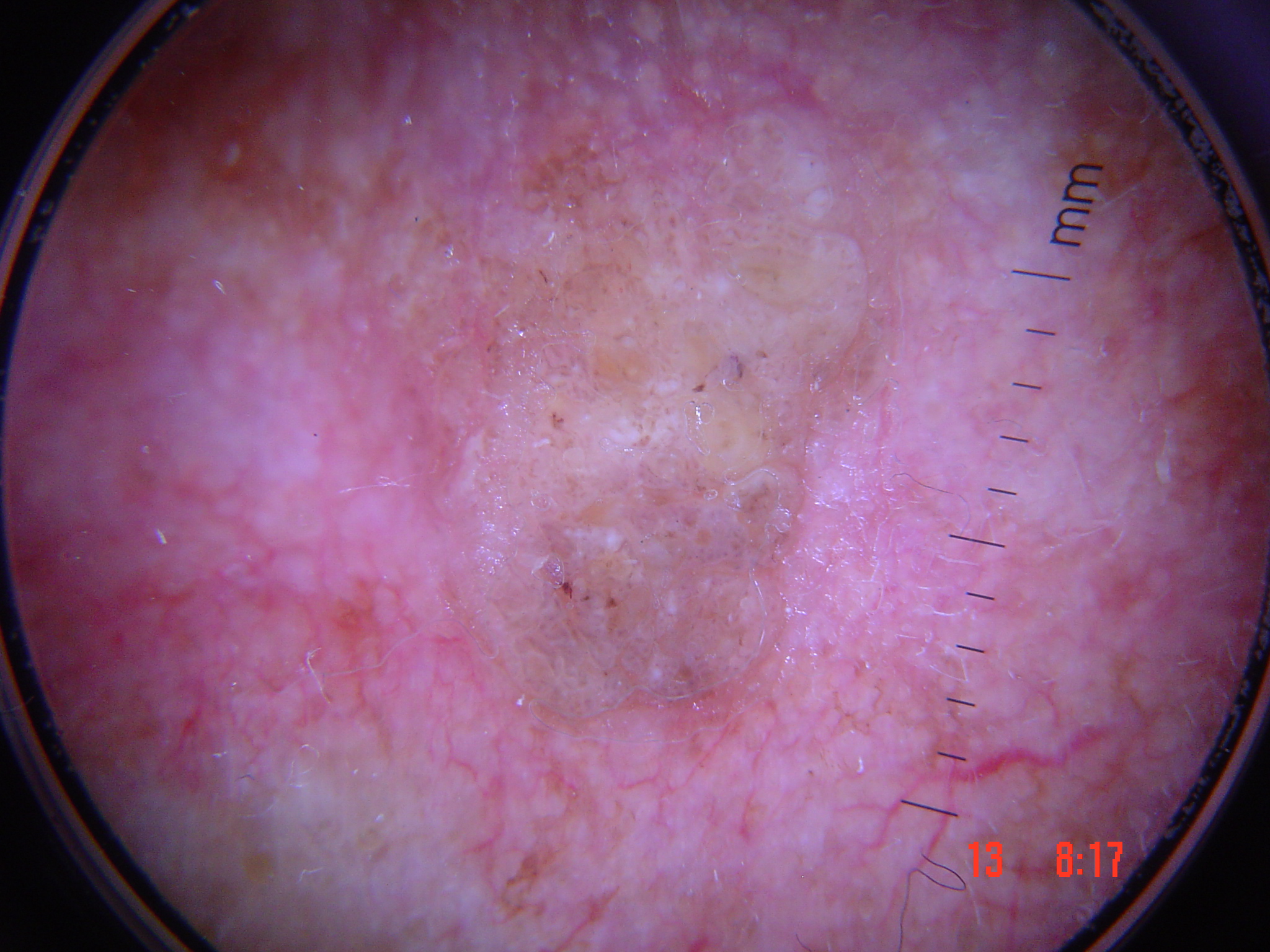lesion type: keratinocytic | diagnosis: seborrheic keratosis (expert consensus).